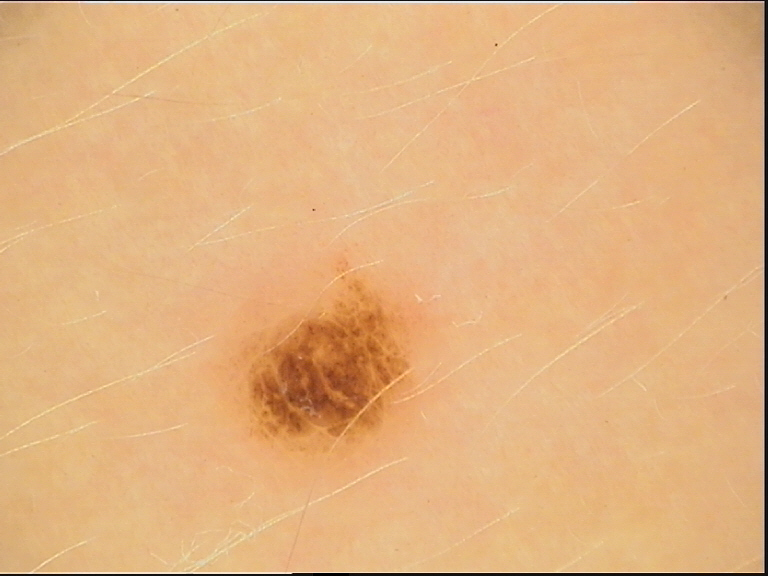Classified as a compound nevus.